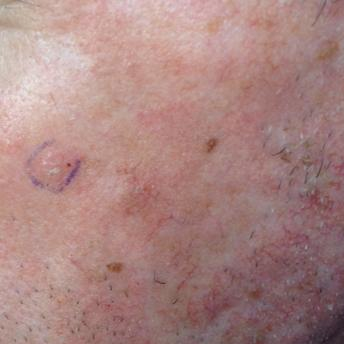A patient in their early 50s. The lesion was found on the face. Consistent with an actinic keratosis.